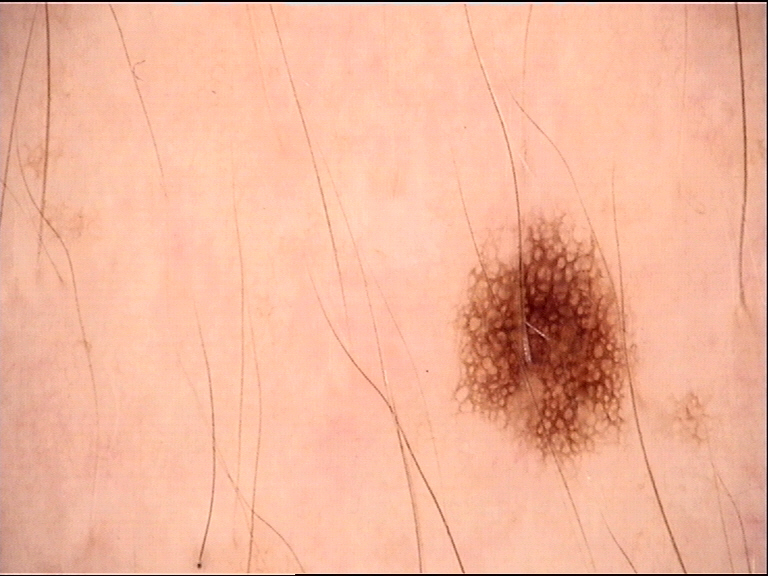Findings: A dermoscopic photograph of a skin lesion. Impression: Diagnosed as a junctional nevus.